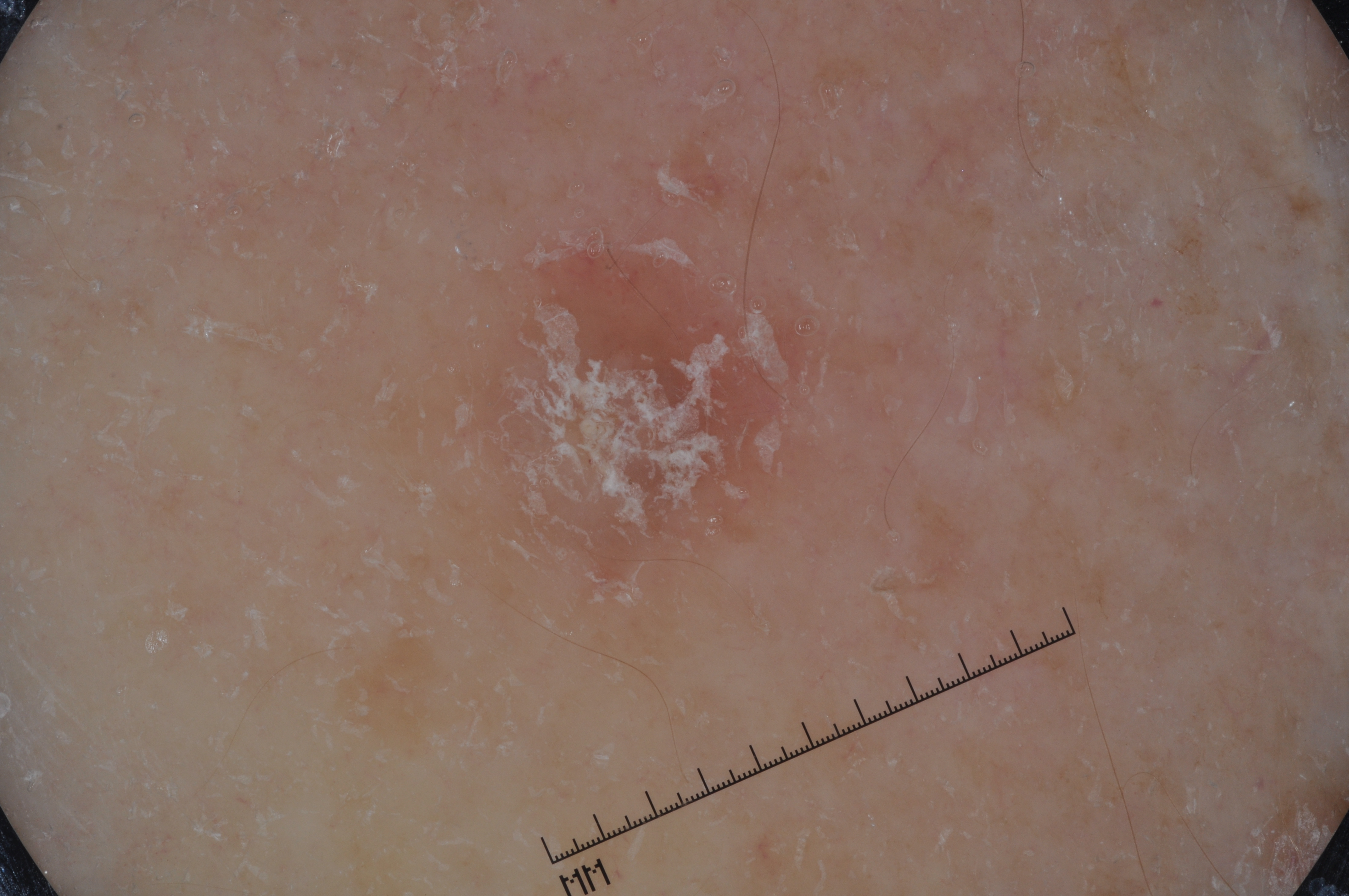A dermoscopic view of a skin lesion. In (x1, y1, x2, y2) order, the lesion is located at 474 158 872 601. Dermoscopic examination shows no streaks, negative network, milia-like cysts, or pigment network. The diagnostic assessment was a seborrheic keratosis, a keratinocytic lesion.